A dermoscopic close-up of a skin lesion.
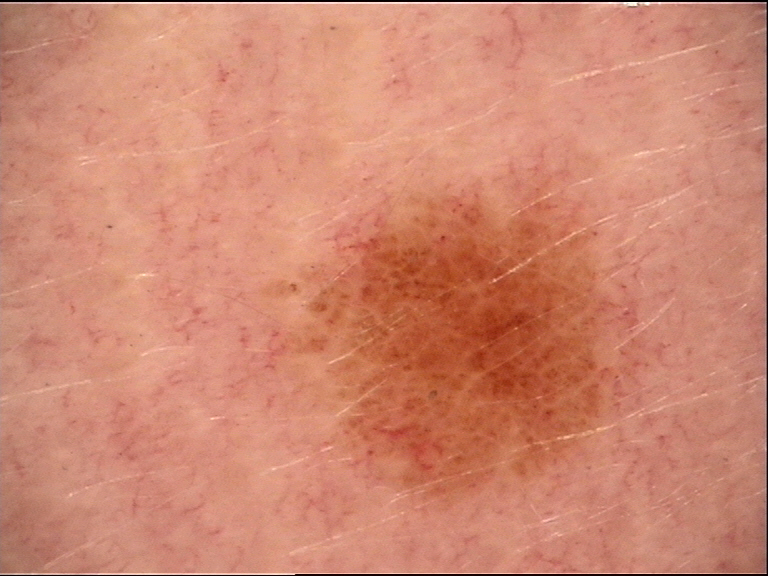Findings:
- assessment — dysplastic junctional nevus (expert consensus)